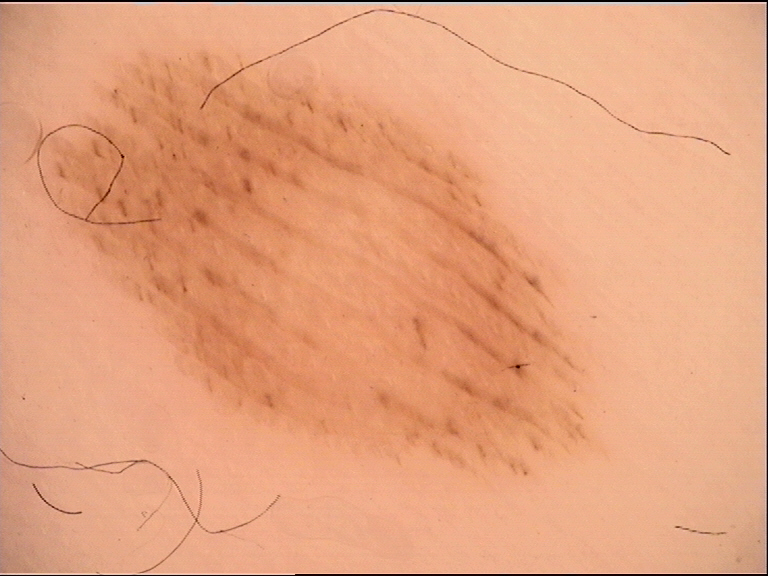{
  "lesion_type": {
    "main_class": "banal",
    "pattern": "junctional"
  },
  "diagnosis": {
    "name": "acral junctional nevus",
    "code": "ajb",
    "malignancy": "benign",
    "super_class": "melanocytic",
    "confirmation": "expert consensus"
  }
}